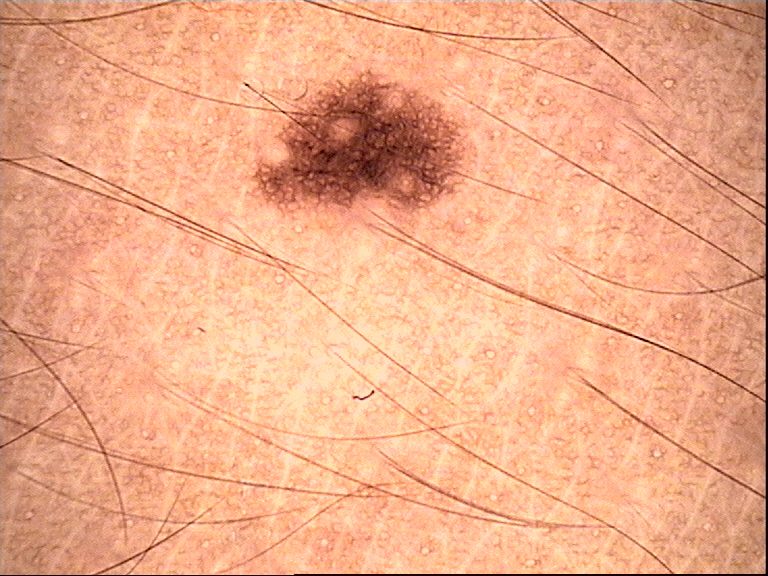Impression:
Classified as a dysplastic junctional nevus.